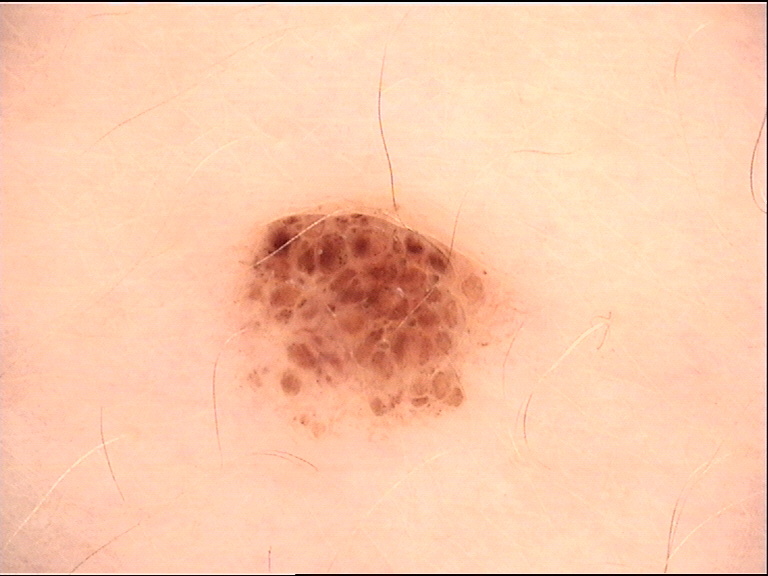| feature | finding |
|---|---|
| class | compound nevus (expert consensus) |